Located on the arm and leg; an image taken at an angle — 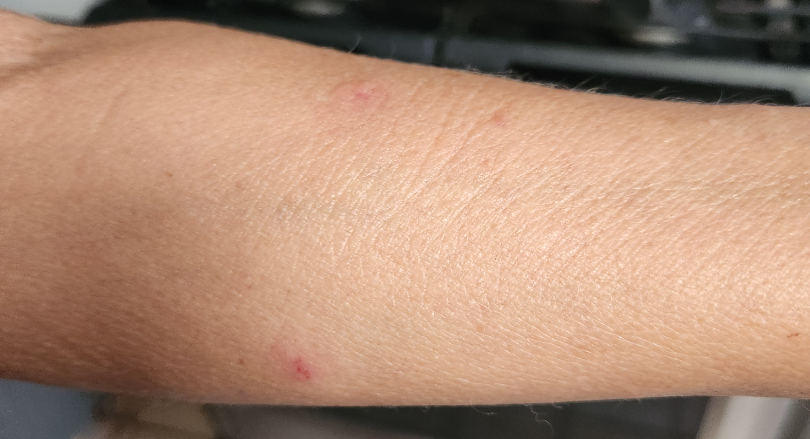Background:
Self-categorized by the patient as a rash. The contributor notes itching. The patient reported no systemic symptoms. Texture is reported as fluid-filled.
Findings:
Animal bite - wound (most likely); Inflicted skin lesions (considered); Eczema (less likely).